A female patient aged 38-42 · a dermoscopic image of a skin lesion: 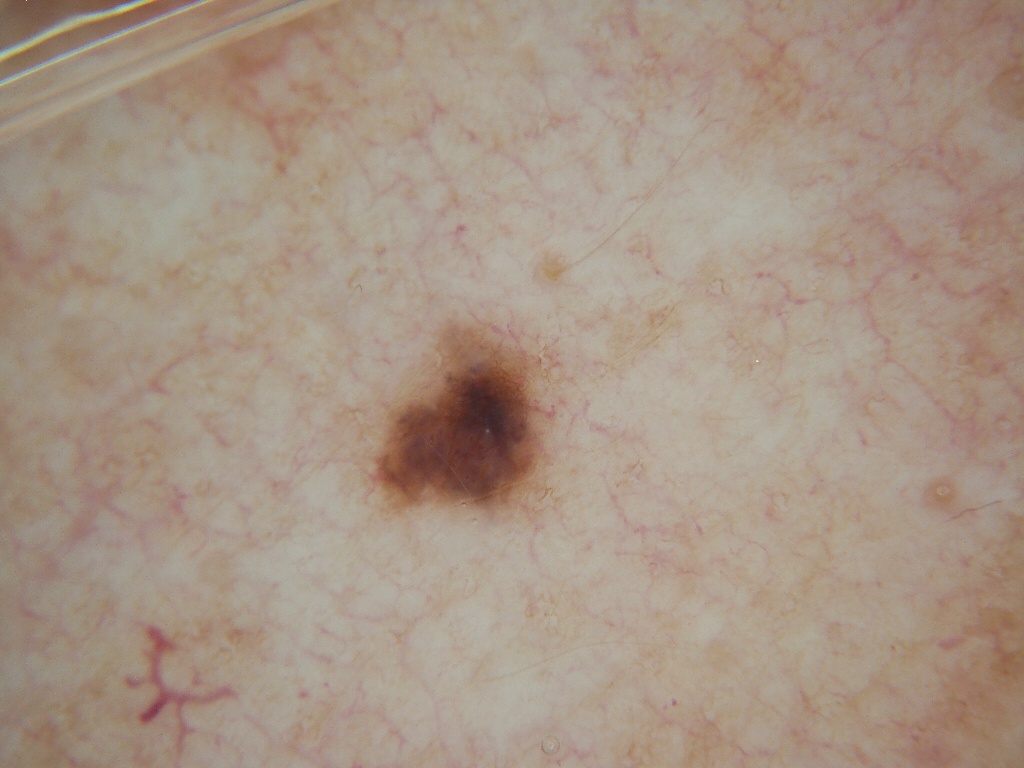dermoscopic pattern — milia-like cysts and pigment network; absent: globules, negative network, and streaks | location — x1=367, y1=320, x2=552, y2=518 | impression — a melanocytic nevus, a benign skin lesion.